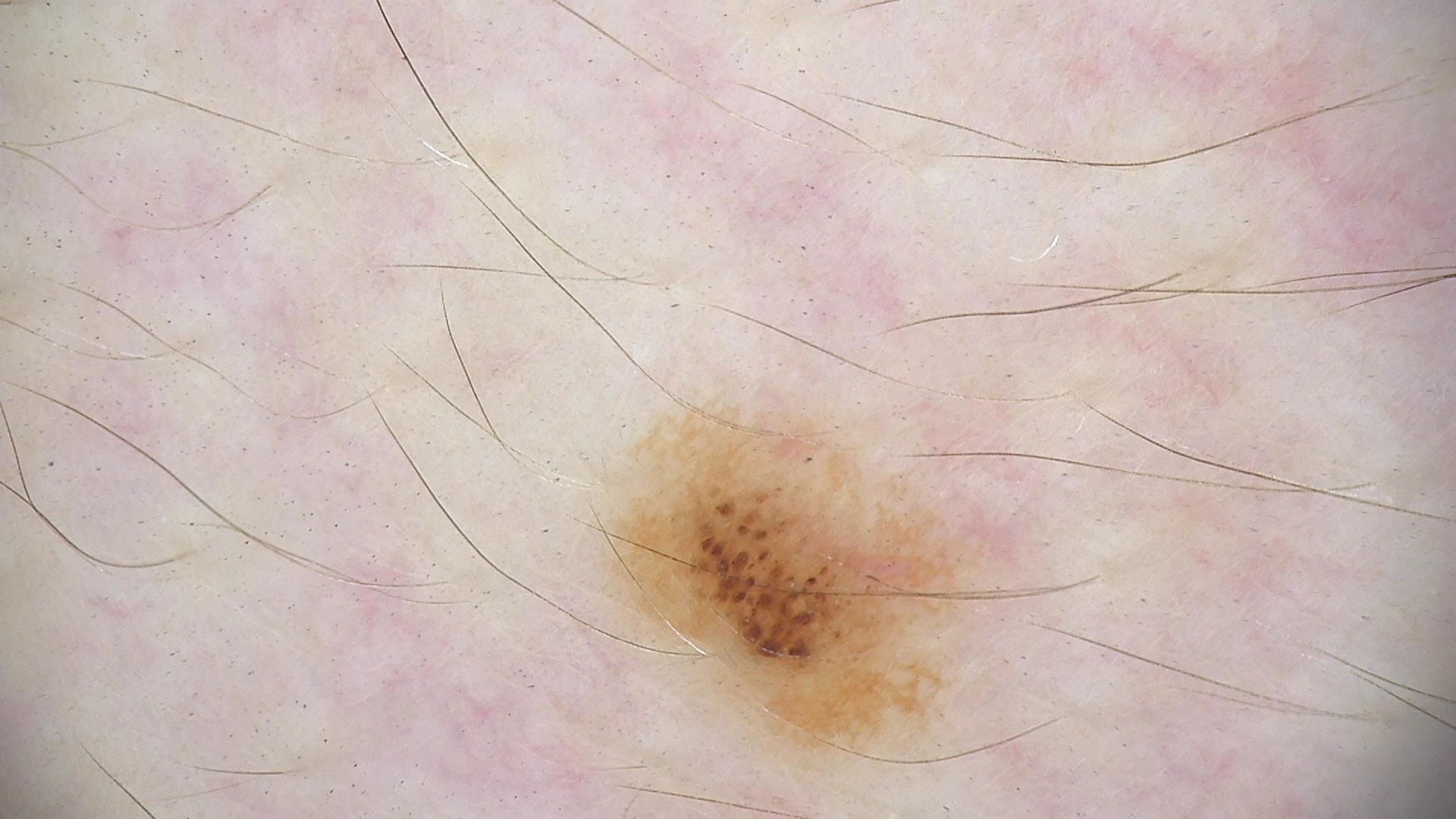Impression:
Labeled as a dysplastic junctional nevus.